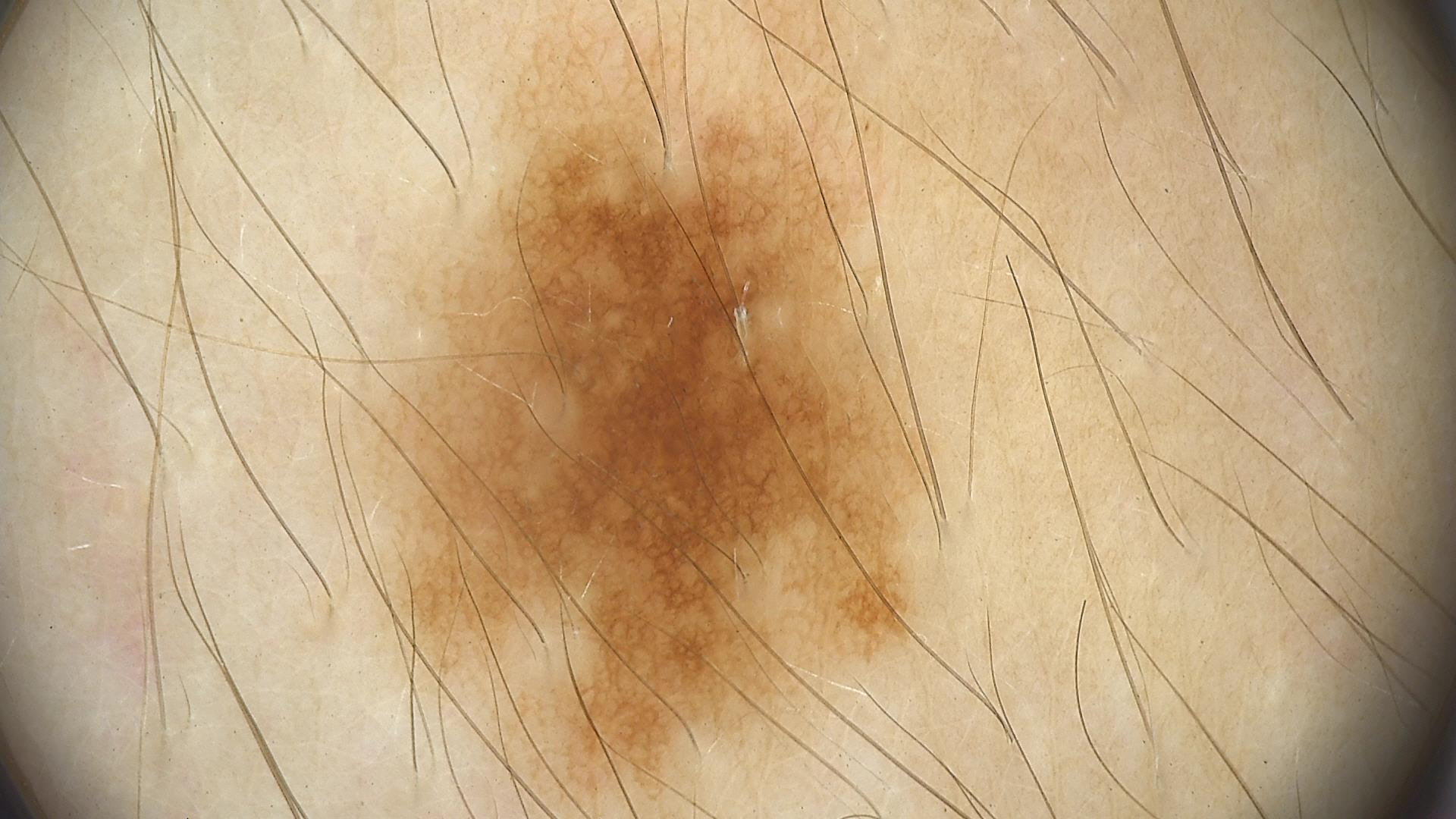| field | value |
|---|---|
| subtype | banal |
| assessment | junctional nevus (expert consensus) |